A clinical photograph of a skin lesion · a male subject 71 years old · the patient is FST II.
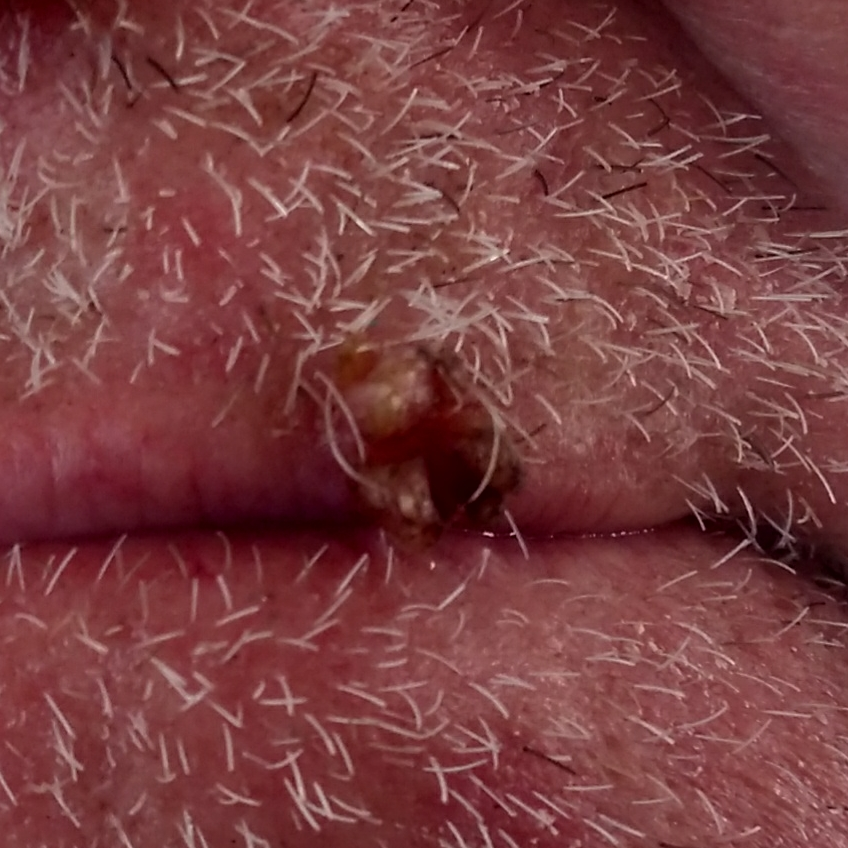{"lesion_location": "a lip", "lesion_size": {"diameter_1_mm": 6.0, "diameter_2_mm": 5.0}, "diagnosis": {"name": "actinic keratosis", "code": "ACK", "malignancy": "indeterminate", "confirmation": "histopathology"}}